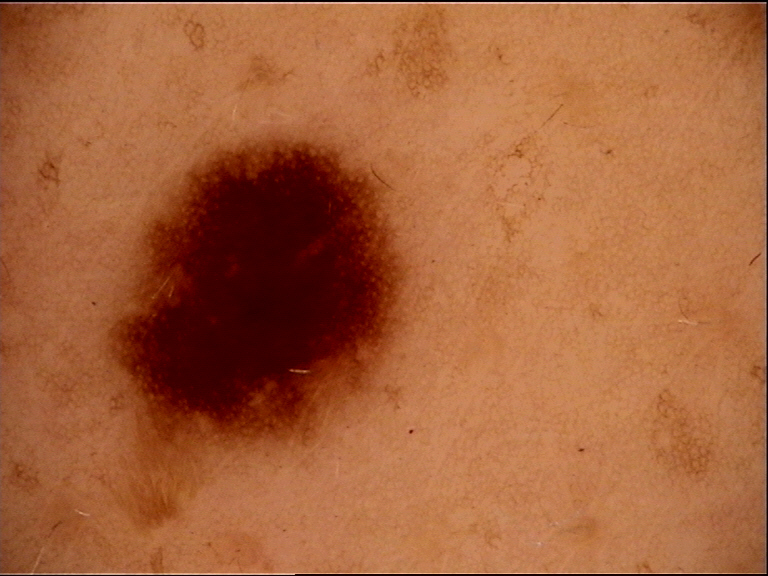Q: What is the imaging modality?
A: dermatoscopy
Q: What is this lesion?
A: dysplastic junctional nevus (expert consensus)